A dermatoscopic image of a skin lesion.
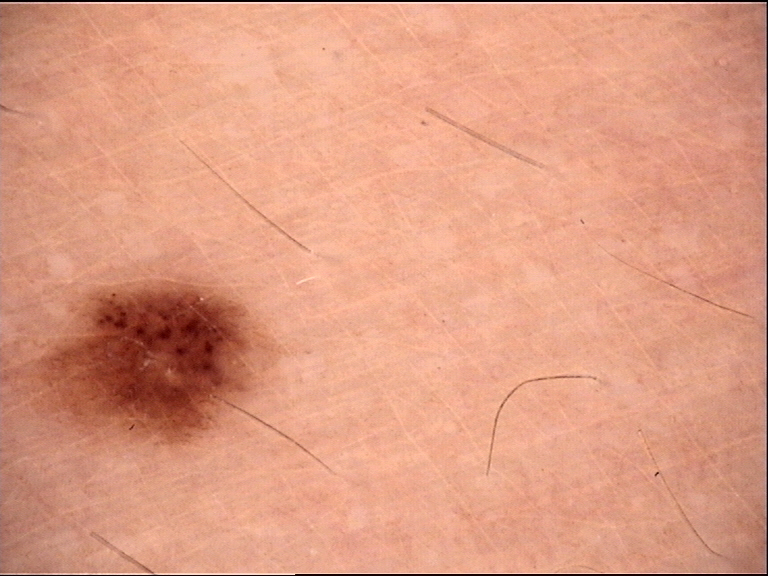Conclusion: Diagnosed as a benign lesion — a dysplastic junctional nevus.